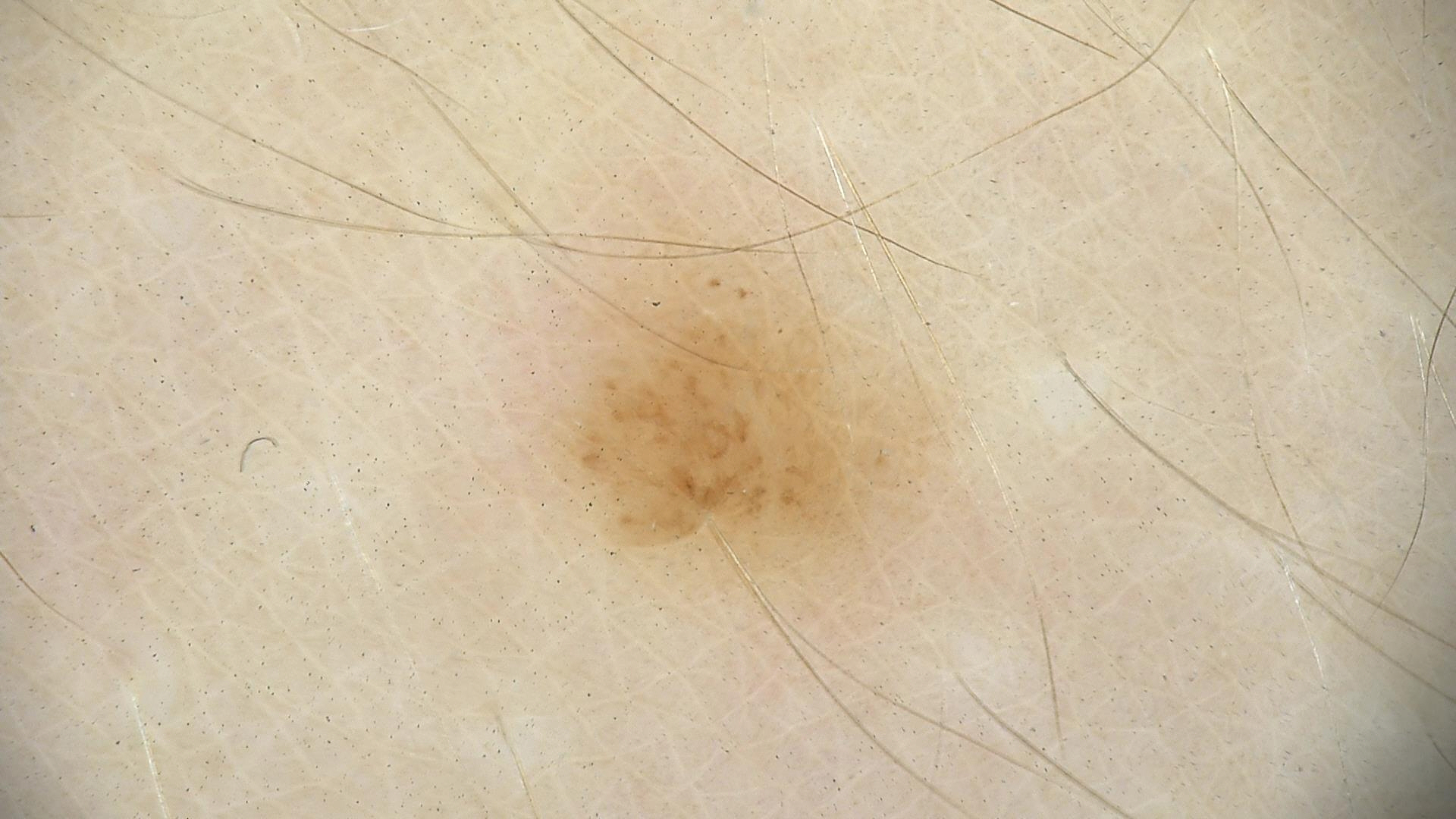A skin lesion imaged with a dermatoscope. The diagnostic label was a benign lesion — a dysplastic junctional nevus.